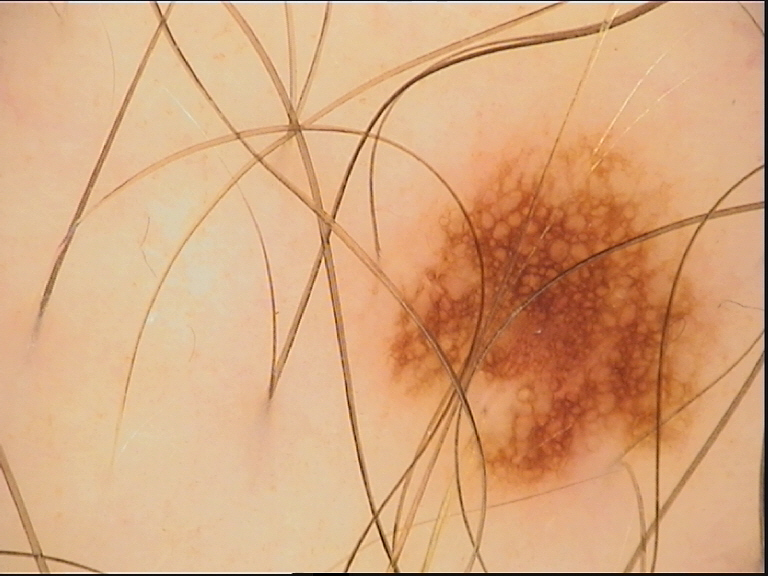diagnosis:
  name: dysplastic junctional nevus
  code: jd
  malignancy: benign
  super_class: melanocytic
  confirmation: expert consensus